A dermoscopy image of a single skin lesion — 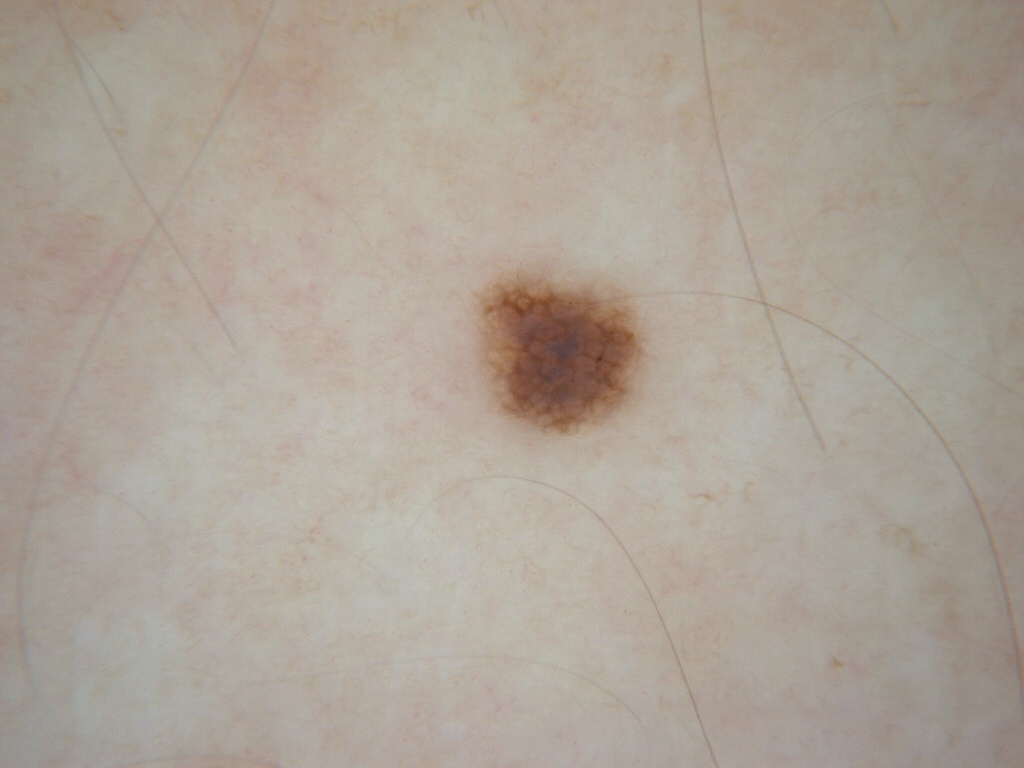Dermoscopic review identifies neither streaks nor globules.
Lesion location: x1=476 y1=269 x2=645 y2=433.
The clinical diagnosis was a benign lesion.